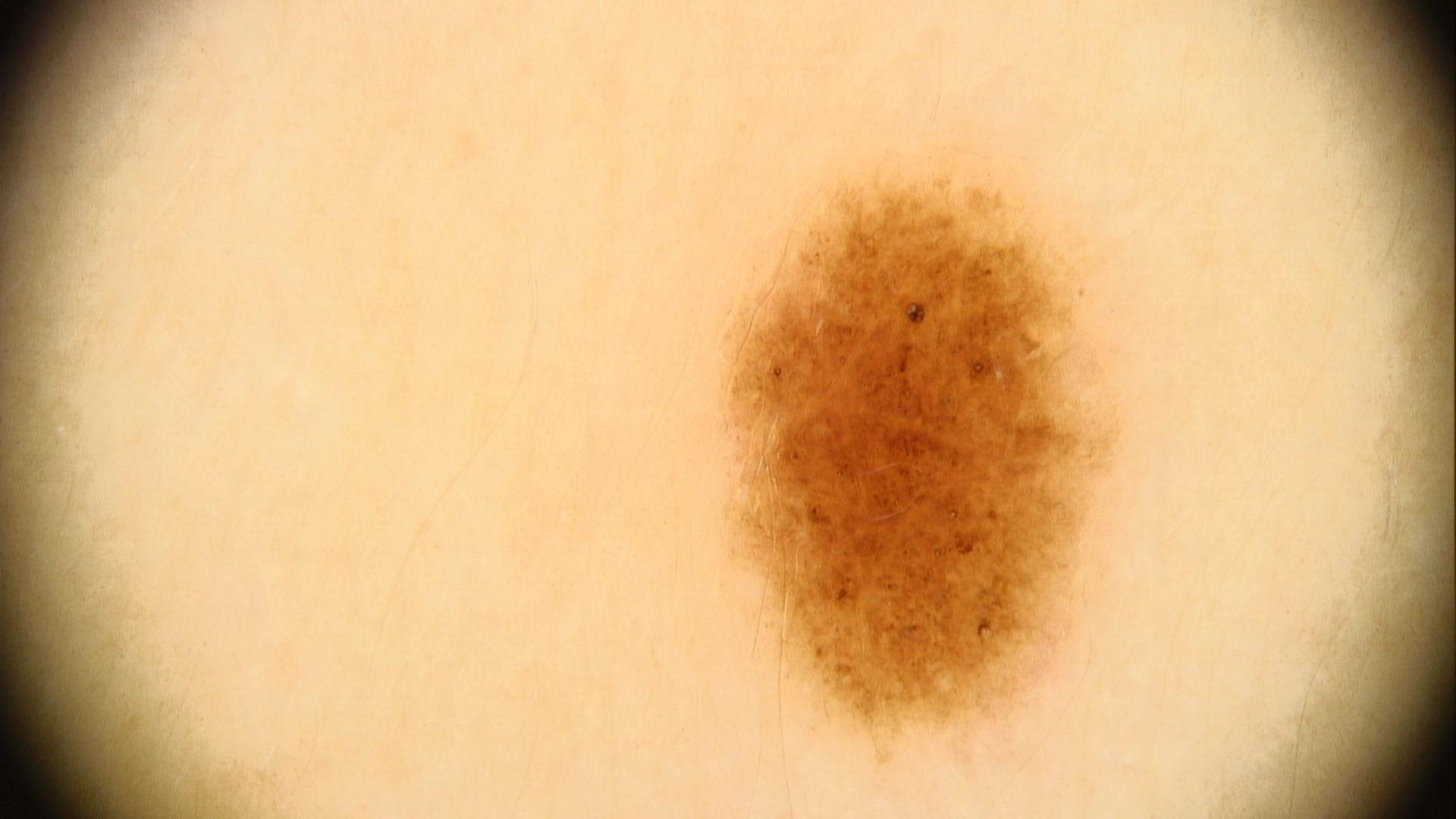A male patient aged 38 to 42.
A dermoscopic image of a skin lesion.
The patient was assessed as skin type III.
The chart records a first-degree relative with melanoma but no previous melanoma.
The lesion was found on the anterior trunk.
The diagnostic impression was a benign lesion — a nevus.